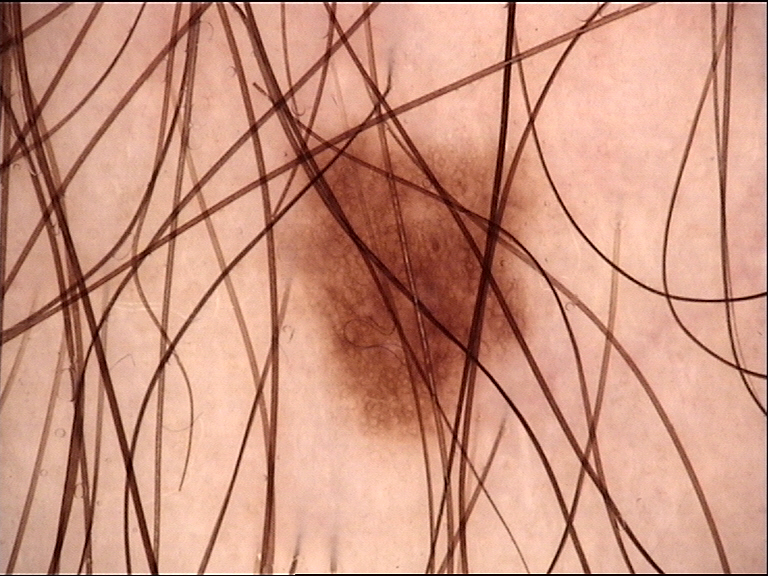{
  "image": "dermoscopy",
  "diagnosis": {
    "name": "dysplastic junctional nevus",
    "code": "jd",
    "malignancy": "benign",
    "super_class": "melanocytic",
    "confirmation": "expert consensus"
  }
}